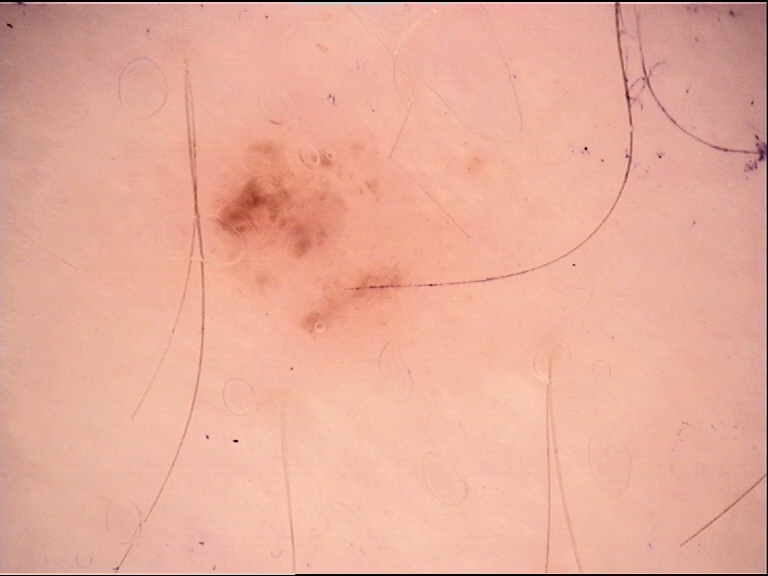A dermoscopic image of a skin lesion. The diagnosis was a benign lesion — a dysplastic junctional nevus.